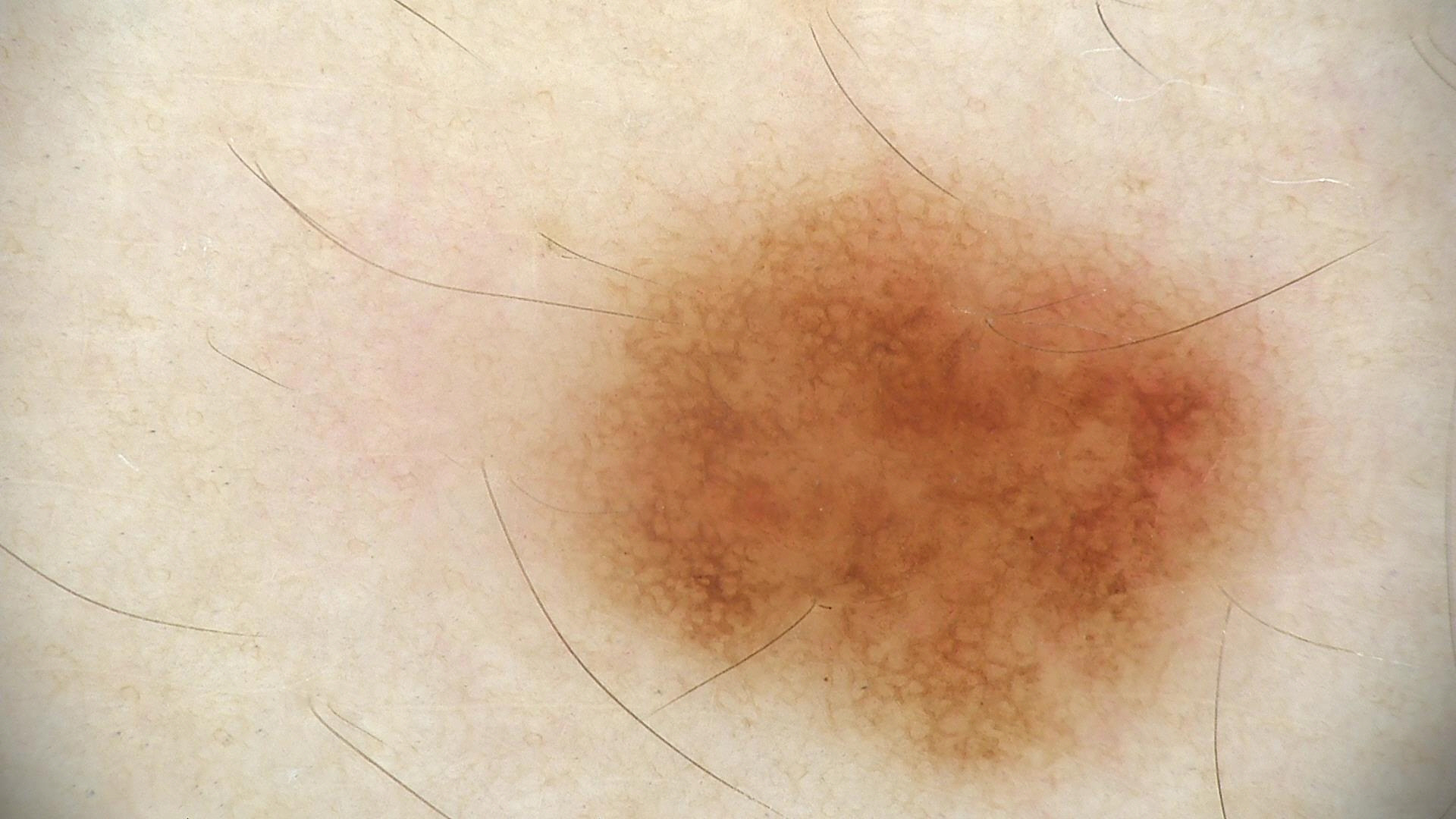Findings:
- class — dysplastic junctional nevus (expert consensus)